This is a dermoscopic photograph of a skin lesion:
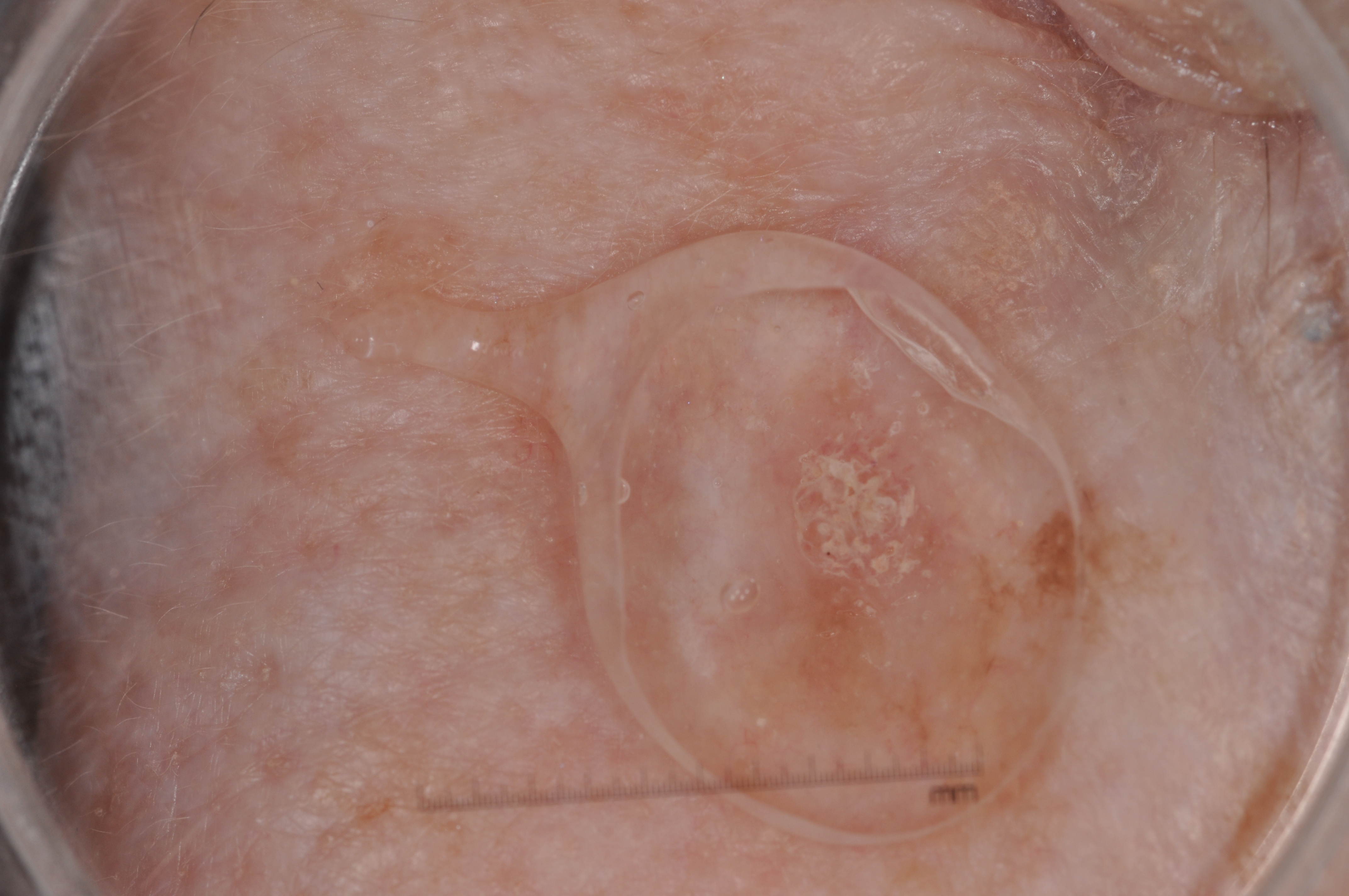dermoscopic features — milia-like cysts; absent: negative network, streaks, and pigment network | location — box(782, 430, 955, 621) | extent — small | impression — a seborrheic keratosis.